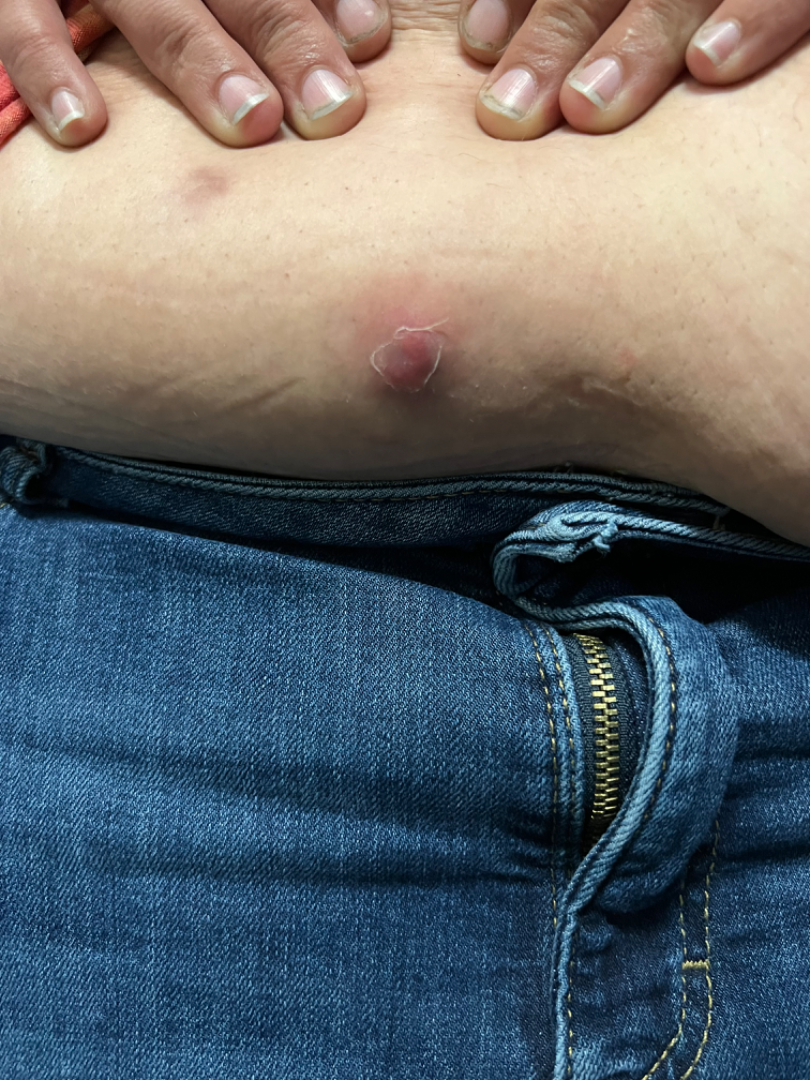A close-up photograph.
The patient is female.
The front of the torso and leg are involved.
The leading consideration is Abscess; also consider Skin cancer; also raised was Hidradenitis.